A dermoscopic image of a skin lesion; a female subject aged around 50; per the chart, a previous melanoma:
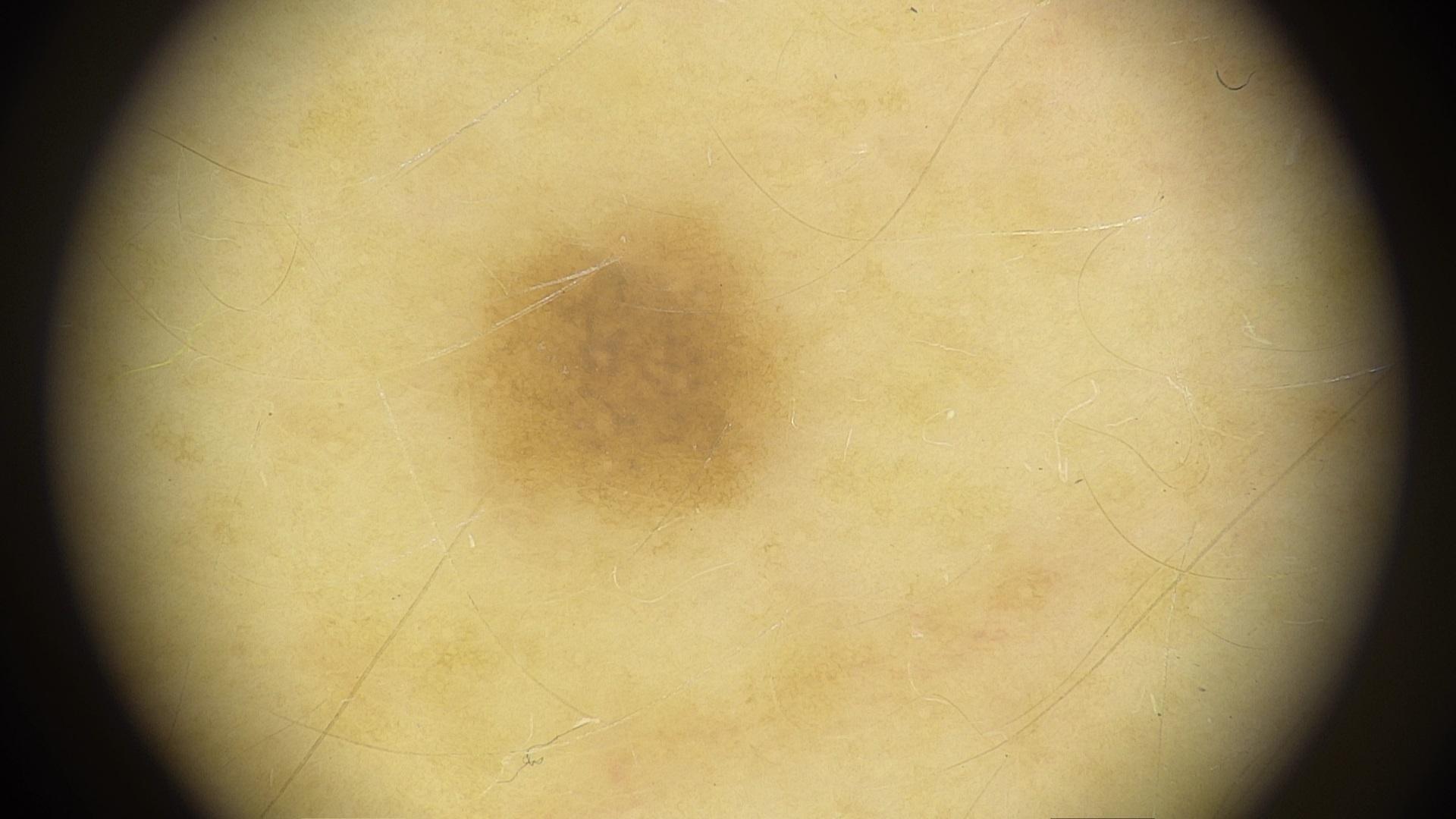Q: What is the anatomic site?
A: the trunk (the posterior trunk)
Q: What is this lesion?
A: Nevus (clinical impression)